Reported duration is one to four weeks. The photo was captured at a distance. Fitzpatrick skin type I. The patient is female. No constitutional symptoms were reported. Located on the top or side of the foot. The contributor notes the lesion is raised or bumpy: 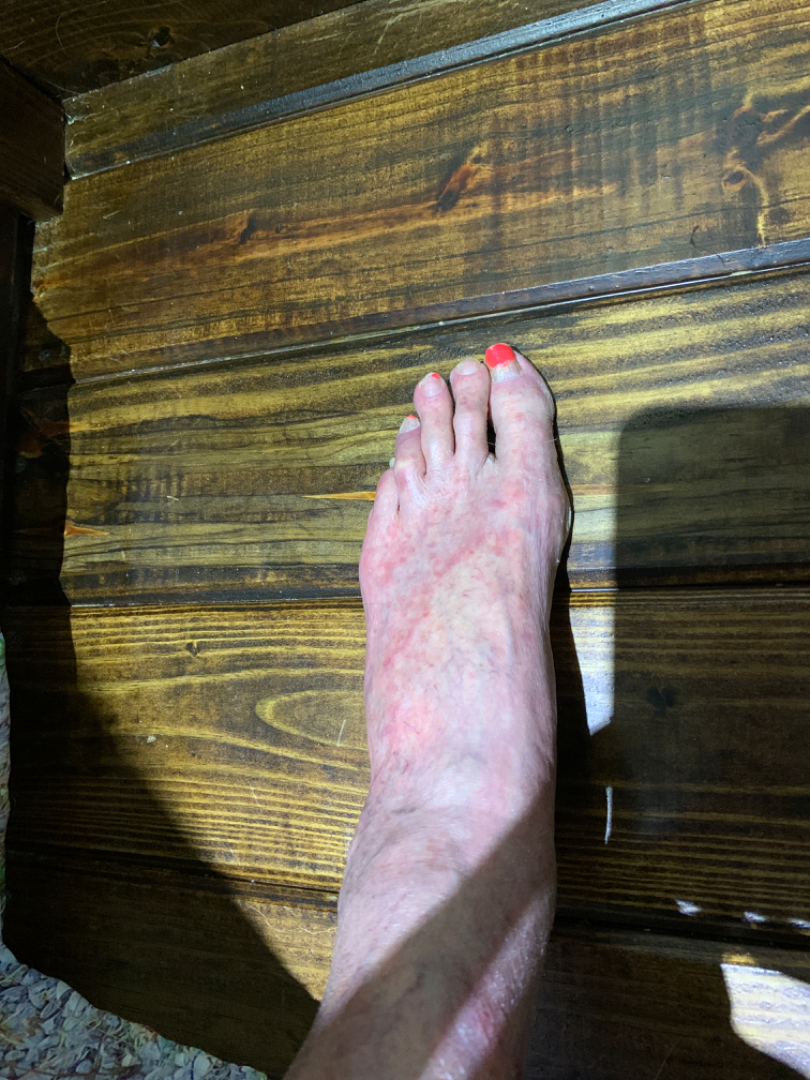On dermatologist assessment of the image: in keeping with Tinea.